A subject in their early 70s — 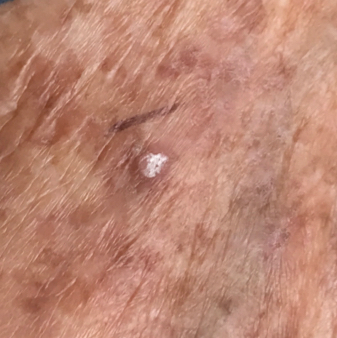Q: Any reported symptoms?
A: itching / no elevation, no bleeding
Q: What is the diagnosis?
A: actinic keratosis (clinical consensus)